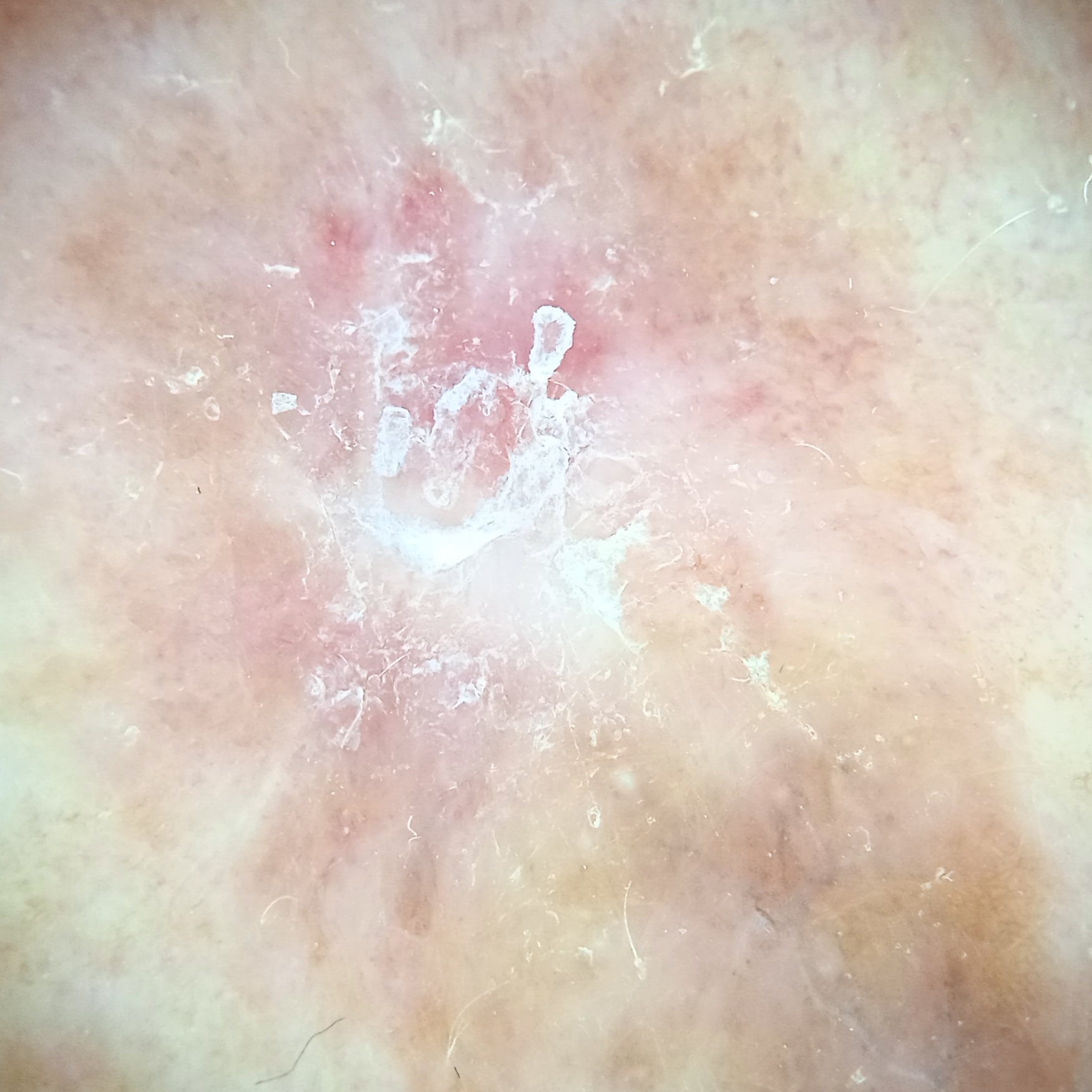Summary:
By self-report, no prior organ transplant. The patient says their skin reddens with sun exposure. Acquired for a research image collection, with no referral diagnosis. The lesion is on the back.
Conclusion:
The diagnostic impression was a squamous cell carcinoma.